An image taken at an angle · no associated systemic symptoms reported · present for one to three months · the patient considered this a rash · the lesion is associated with bothersome appearance and itching · the leg is involved: 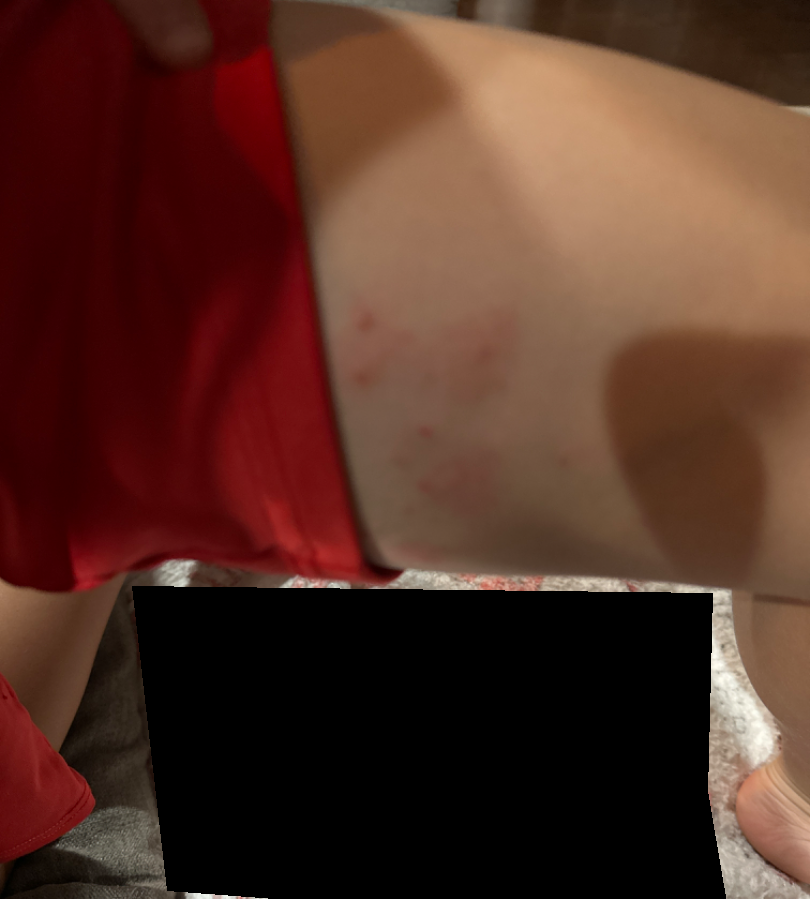Assessment: On dermatologist assessment of the image: most consistent with Molluscum Contagiosum.